A skin lesion imaged with a dermatoscope: 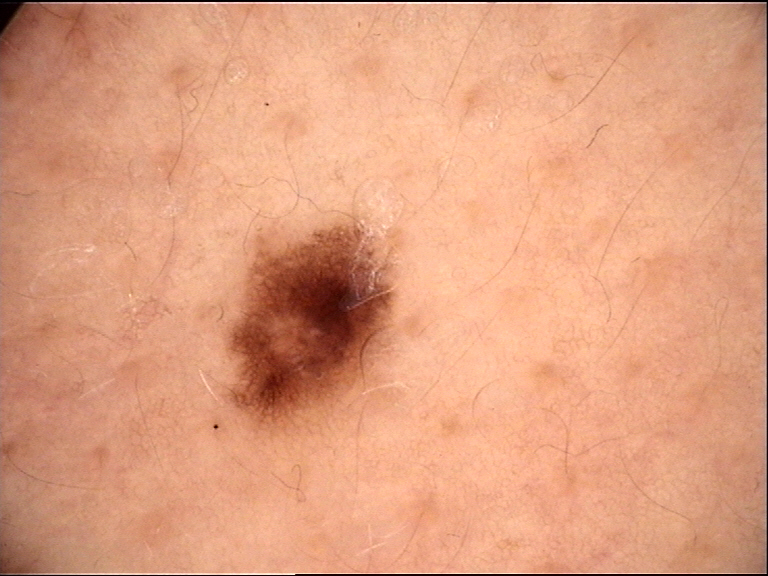The diagnosis was a banal lesion — a junctional nevus.